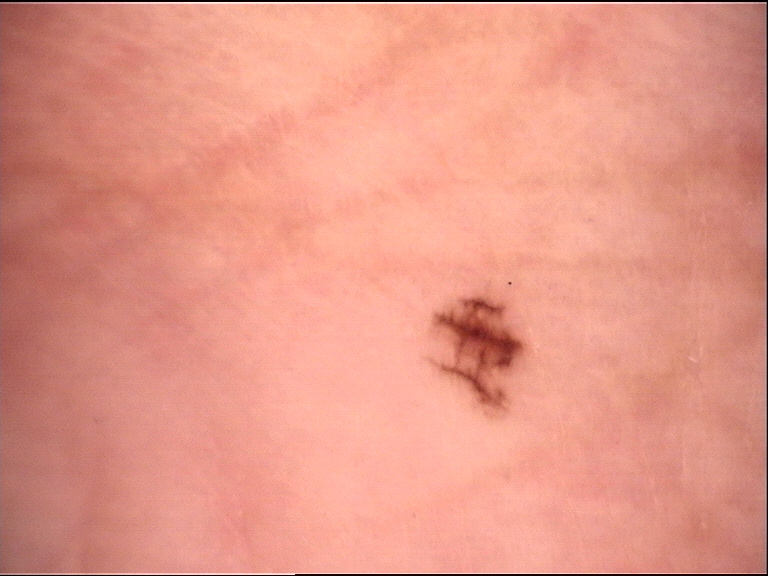imaging — dermatoscopy; class — acral junctional nevus (expert consensus).